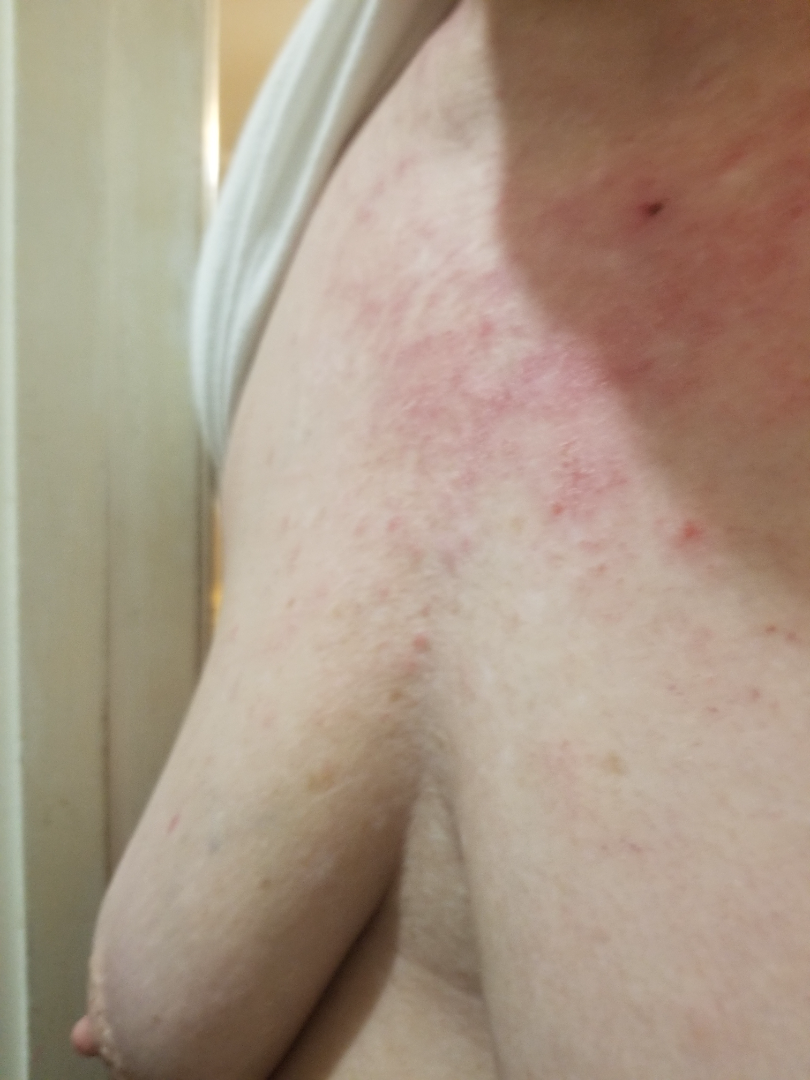<dermatology_case>
<assessment>not assessable</assessment>
<shot_type>close-up</shot_type>
<patient>female, age 60–69</patient>
<skin_tone>
  <fitzpatrick>II</fitzpatrick>
</skin_tone>
<duration>less than one week</duration>
<patient_category>a rash</patient_category>
<systemic_symptoms>fatigue</systemic_symptoms>
<body_site>arm, head or neck, front of the torso</body_site>
<texture>raised or bumpy, fluid-filled</texture>
</dermatology_case>